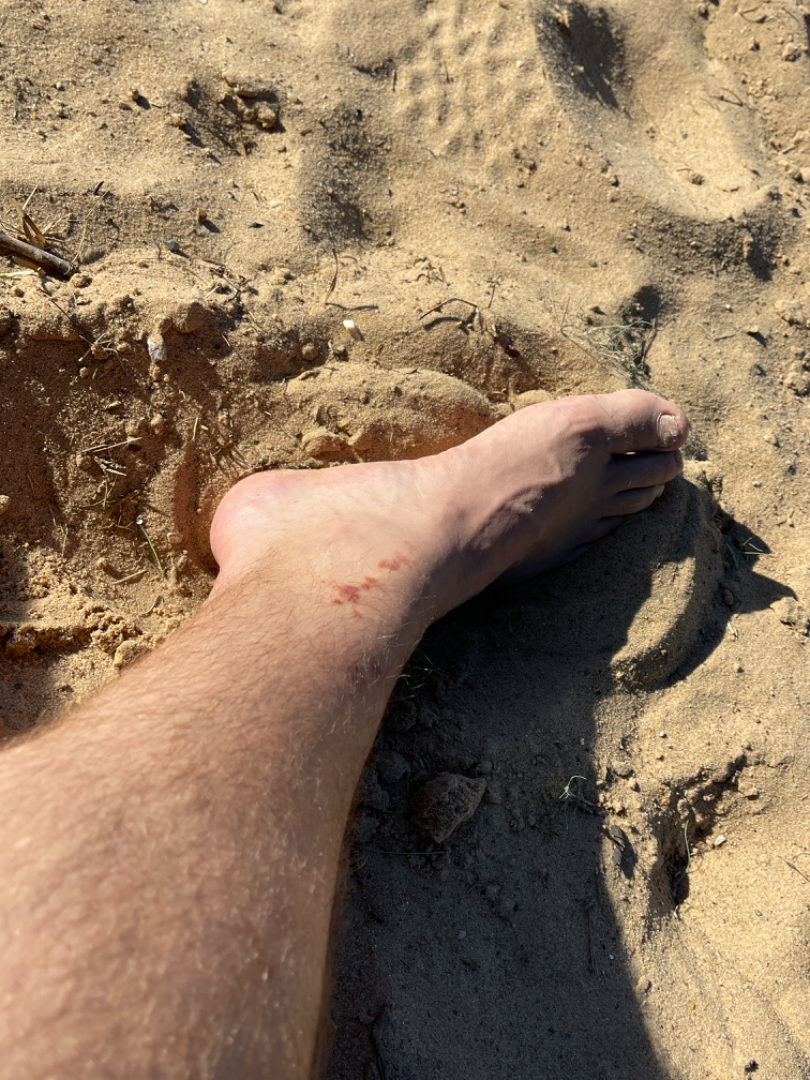The patient notes the lesion is rough or flaky and flat.
The patient reported no systemic symptoms.
The contributor is 30–39, male.
Self-categorized by the patient as a rash.
The photograph was taken at a distance.
Symptoms reported: darkening and bothersome appearance.
The top or side of the foot is involved.
Lichen planus/lichenoid eruption, Pigmented purpuric eruption and Kaposi's sarcoma of skin were each considered, in no particular order.